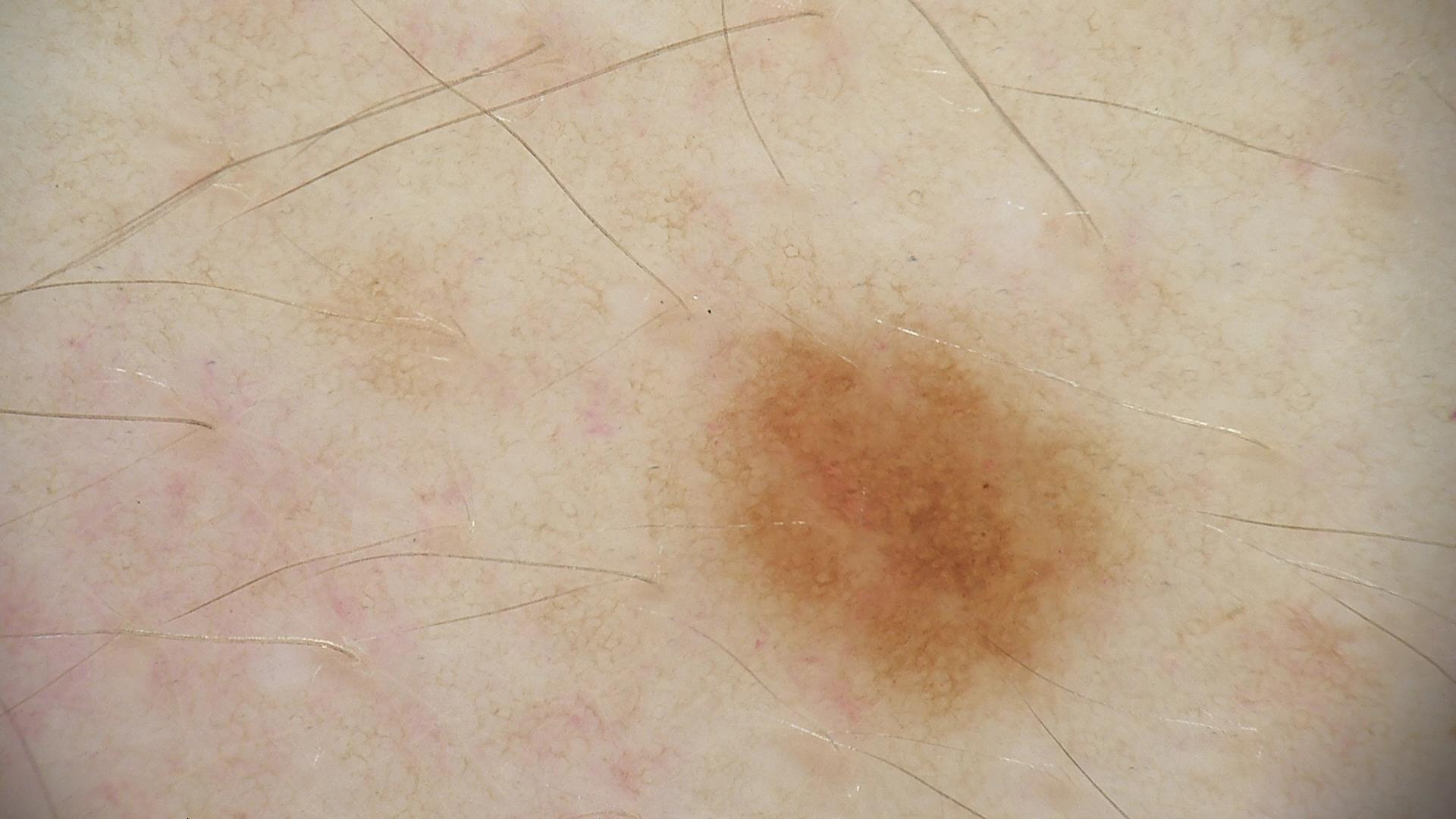Case:
A skin lesion imaged with a dermatoscope.
Impression:
Consistent with a dysplastic junctional nevus.